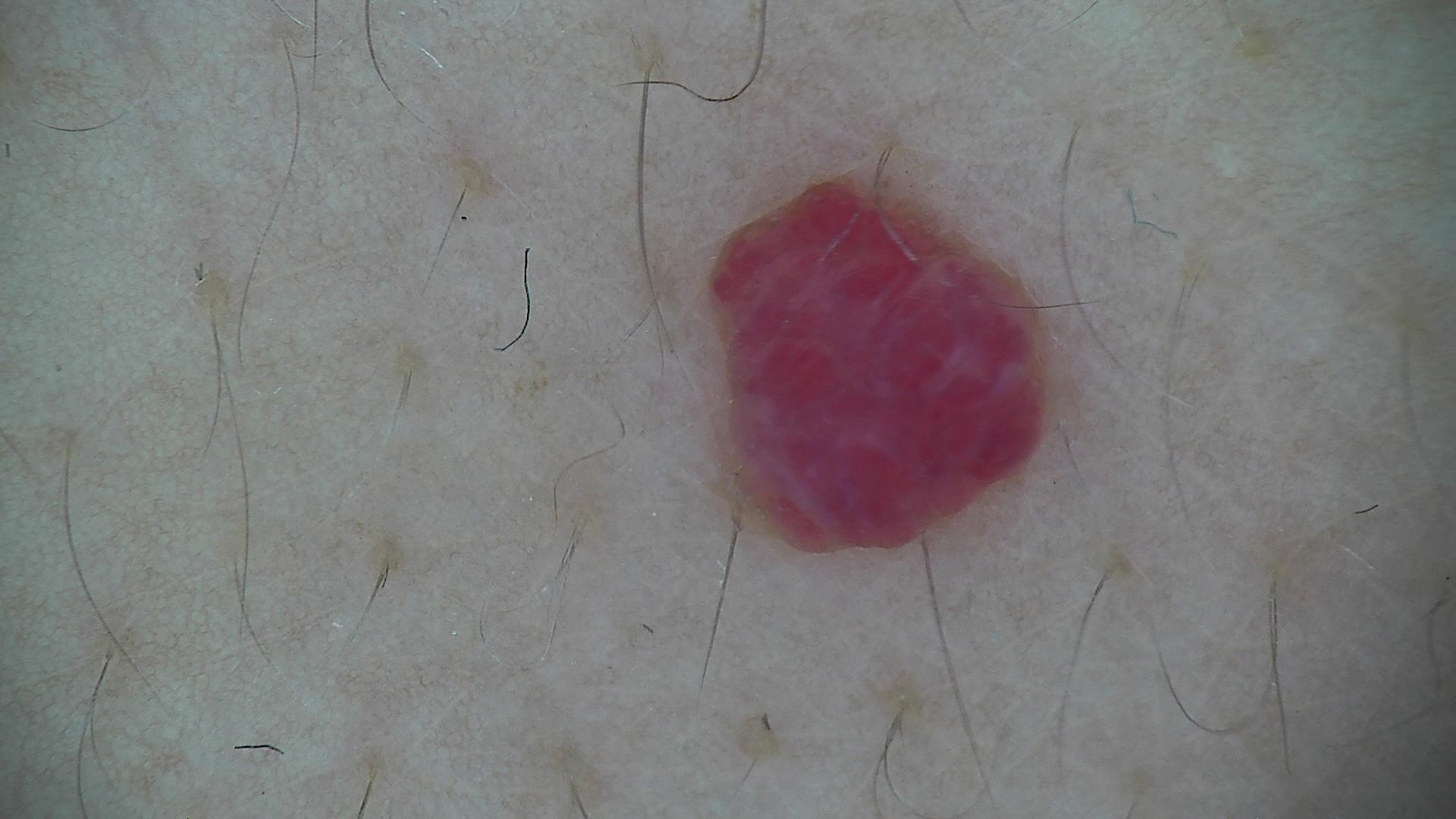The architecture is that of a vascular lesion.
The diagnostic label was a hemangioma.